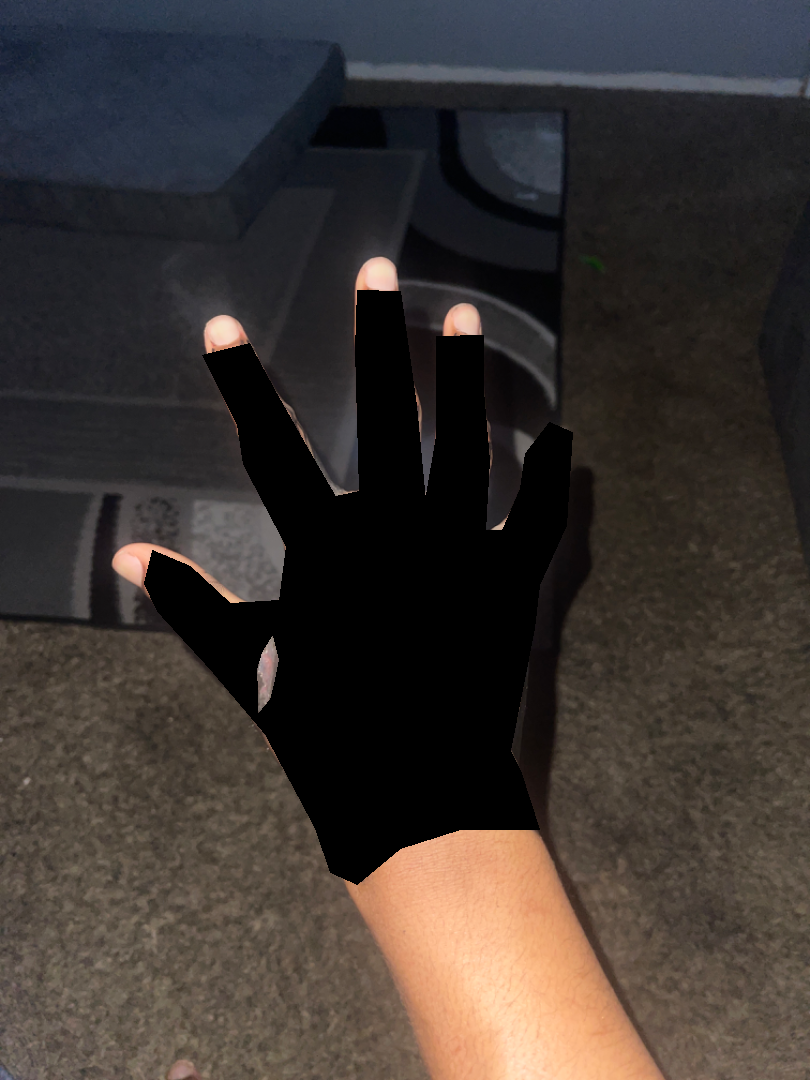The reviewing dermatologist was unable to assign a differential diagnosis from the image. The lesion is described as rough or flaky. The patient described the issue as skin that appeared healthy to them. The back of the hand is involved. The contributor is 18–29, male. No associated systemic symptoms reported. Skin tone: self-reported Fitzpatrick phototype VI. The patient reports the condition has been present for less than one week. The photograph was taken at a distance.